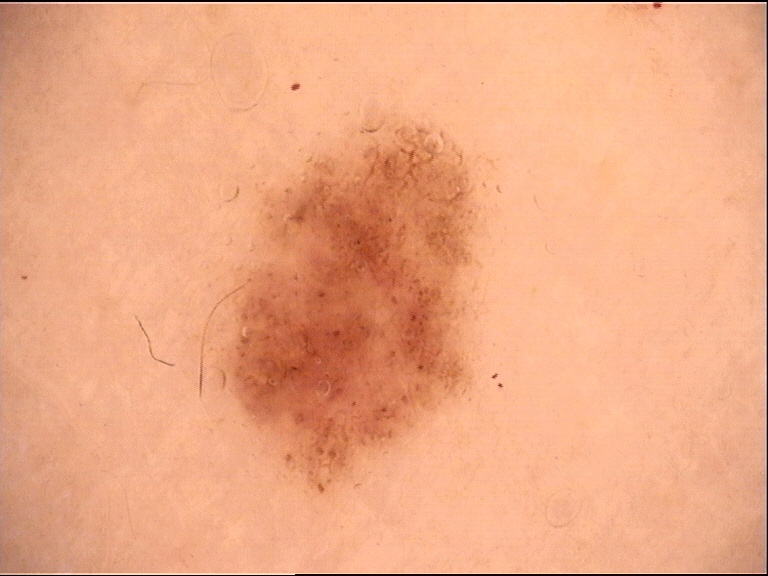modality=dermoscopy | assessment=dysplastic junctional nevus (expert consensus).